This is a close-up image. The affected area is the back of the torso. The contributor is male — 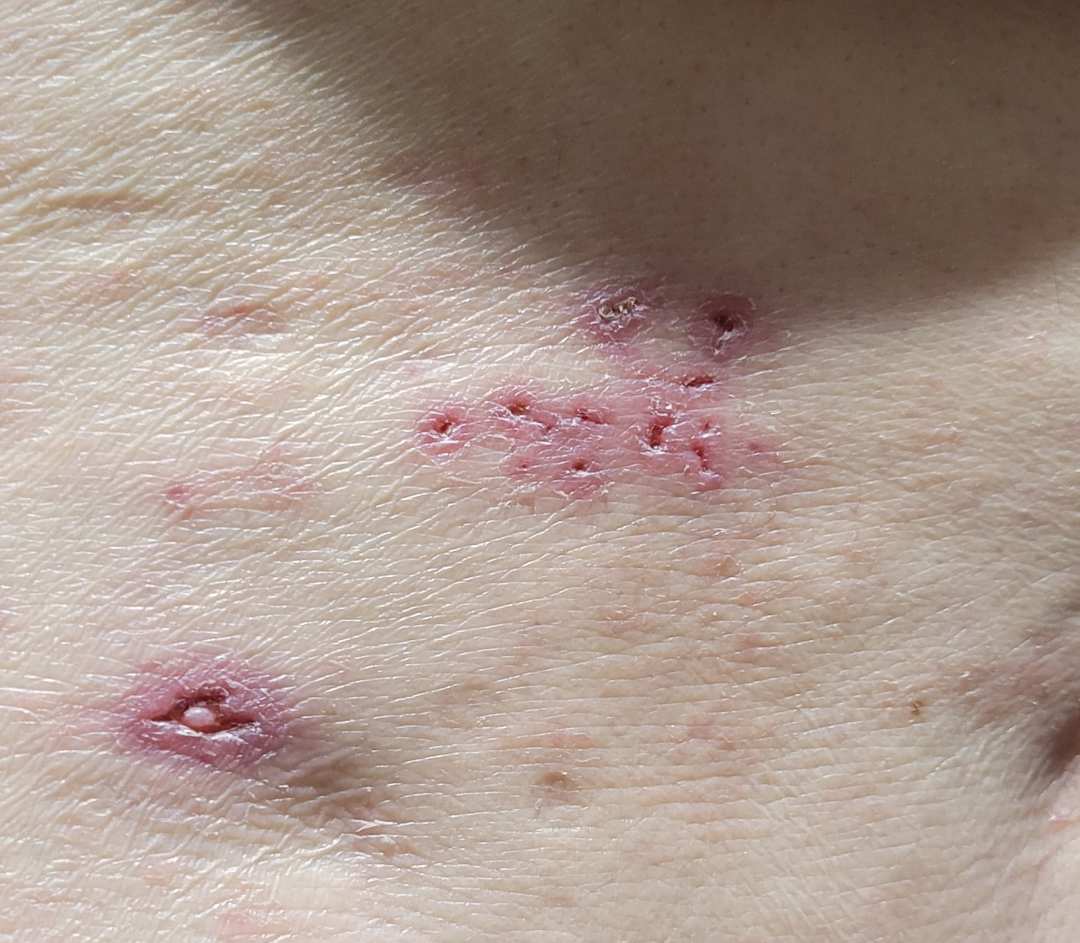assessment = could not be assessed.